A close-up photograph; female patient, age 50–59; the lesion involves the head or neck, arm and leg; reported lesion symptoms include itching, enlargement, pain, burning and bothersome appearance; present for less than one week; the patient indicates associated fatigue and chills; the patient described the issue as a rash:
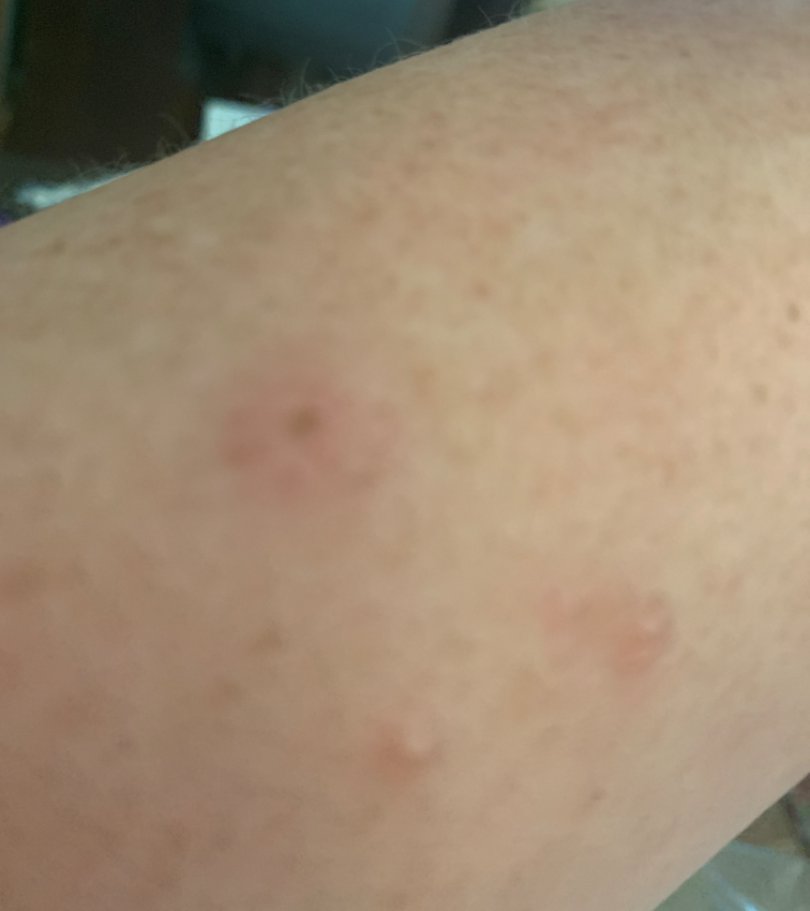The case was difficult to assess from the available photograph.